The photograph is a close-up of the affected area; located on the leg and arm.
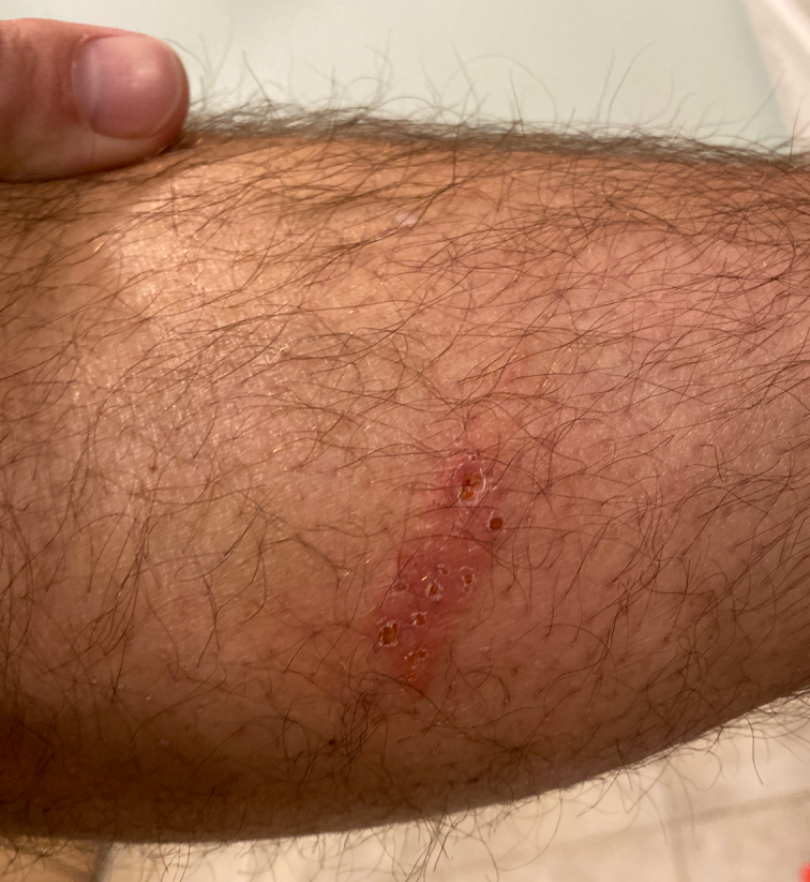{"assessment": "unable to determine"}